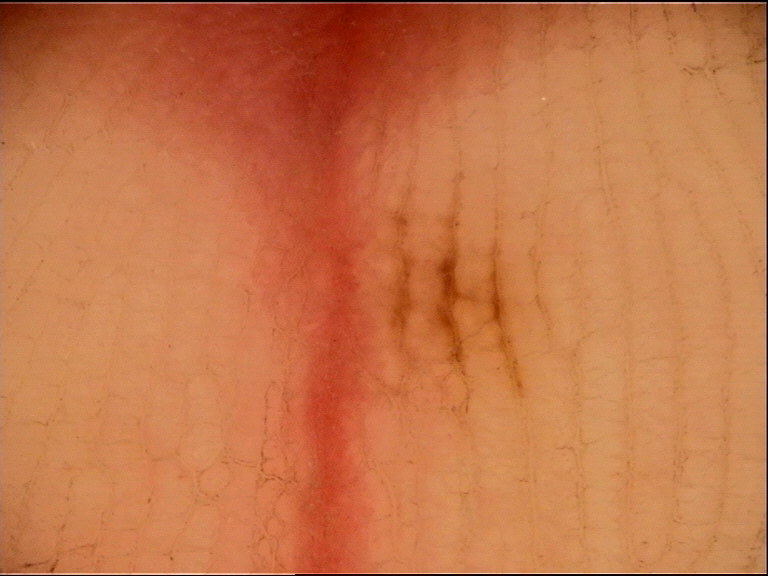Conclusion: The diagnosis was an acral junctional nevus.